An image taken at a distance; the head or neck is involved; the subject is a female aged 18–29:
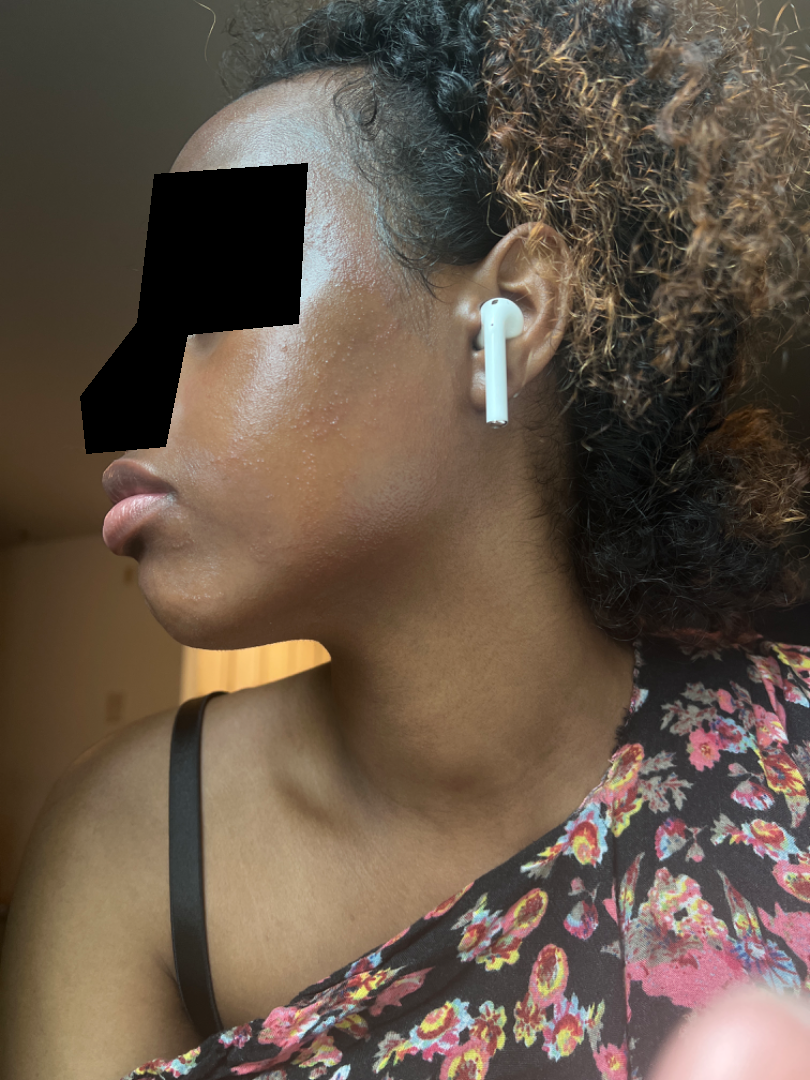The lesion is described as rough or flaky and raised or bumpy.
No relevant systemic symptoms.
The lesion is associated with itching and burning.
Reported duration is about one day.
The patient described the issue as a rash.
Contact dermatitis and Allergic Contact Dermatitis were each considered, in no particular order; less probable is Acne; less likely is Miliaria.